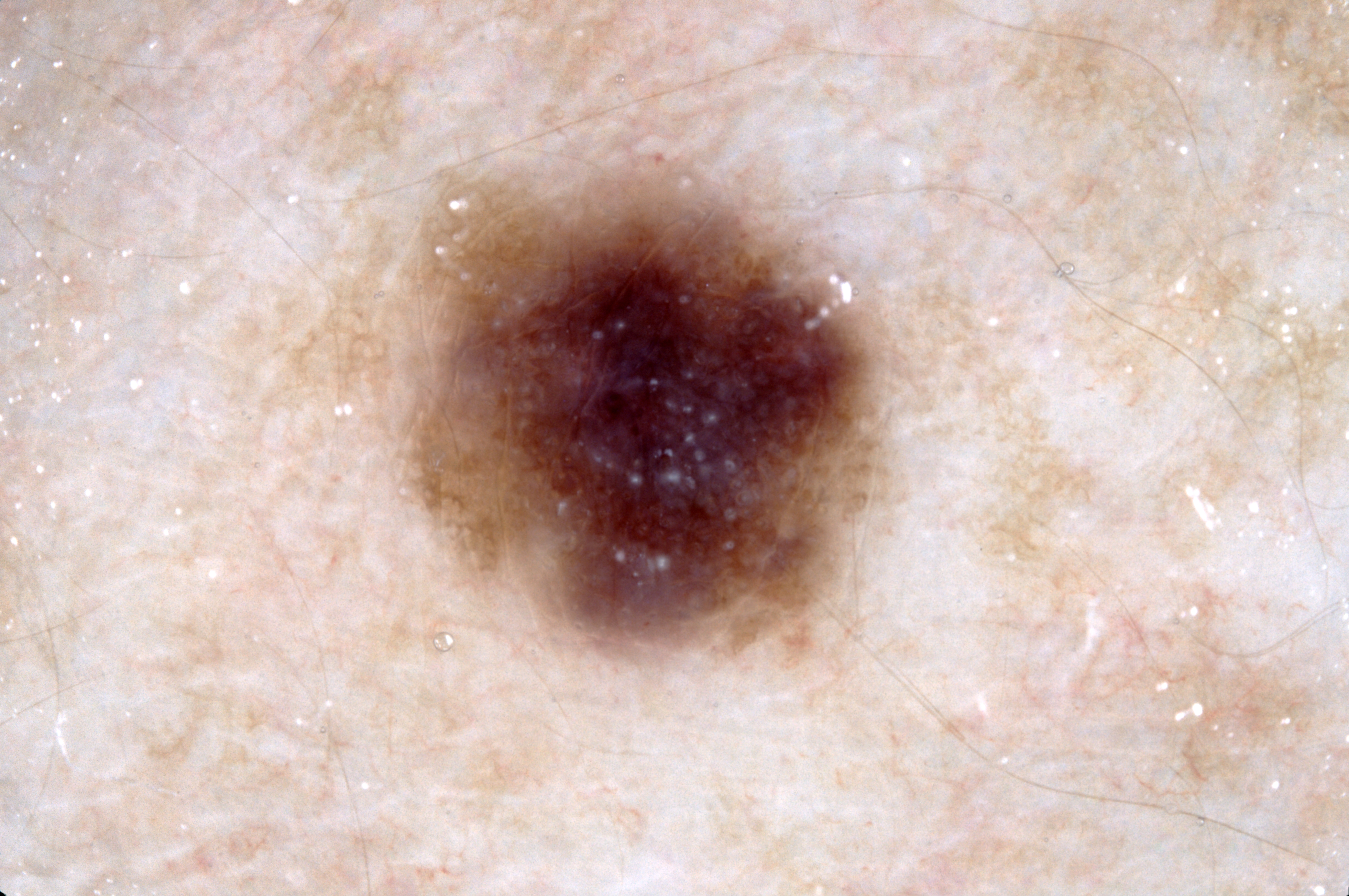<record>
<image>
  <modality>dermoscopy</modality>
</image>
<lesion_location>
  <bbox_xyxy>411, 168, 885, 658</bbox_xyxy>
</lesion_location>
<diagnosis>
  <name>melanocytic nevus</name>
  <malignancy>benign</malignancy>
  <lineage>melanocytic</lineage>
  <provenance>clinical</provenance>
</diagnosis>
</record>